Self-categorized by the patient as a rash. The patient reports the lesion is rough or flaky. The leg is involved. The condition has been present for one to four weeks. No relevant systemic symptoms. The photograph is a close-up of the affected area. Symptoms reported: itching and burning.
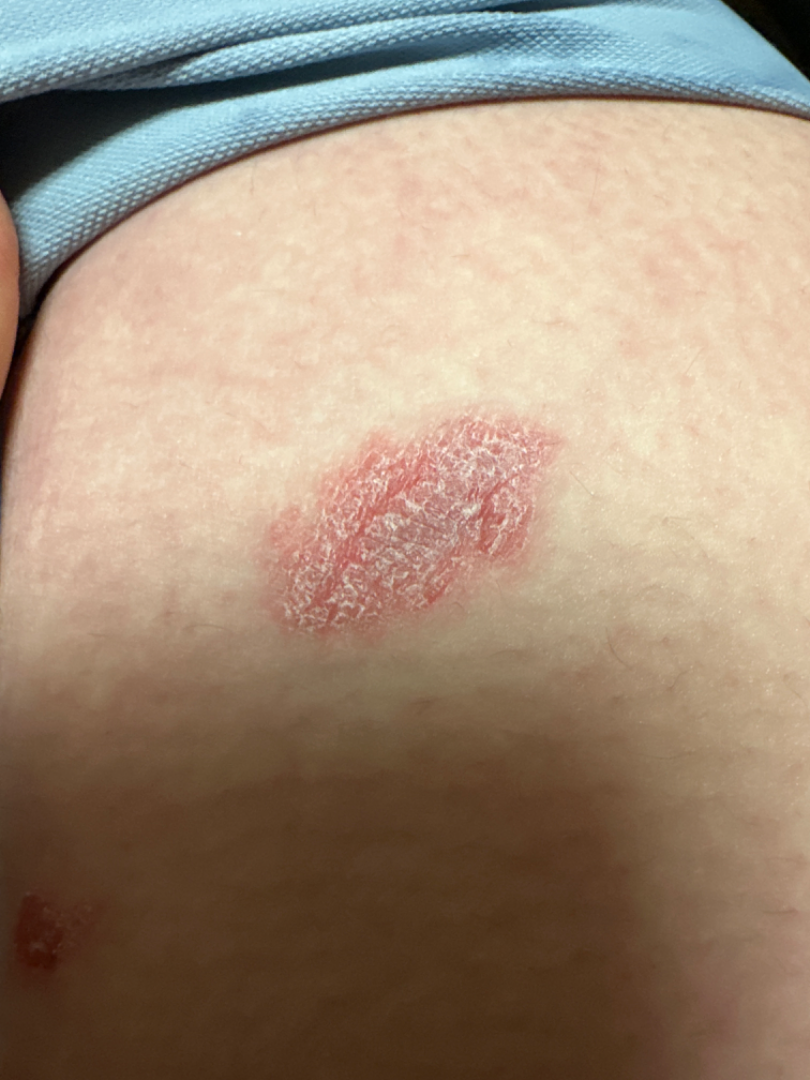The case was difficult to assess from the available photograph.